Reported duration is less than one week, skin tone: lay graders estimated 3 on the MST, symptoms reported: itching, an image taken at an angle, the arm is involved: 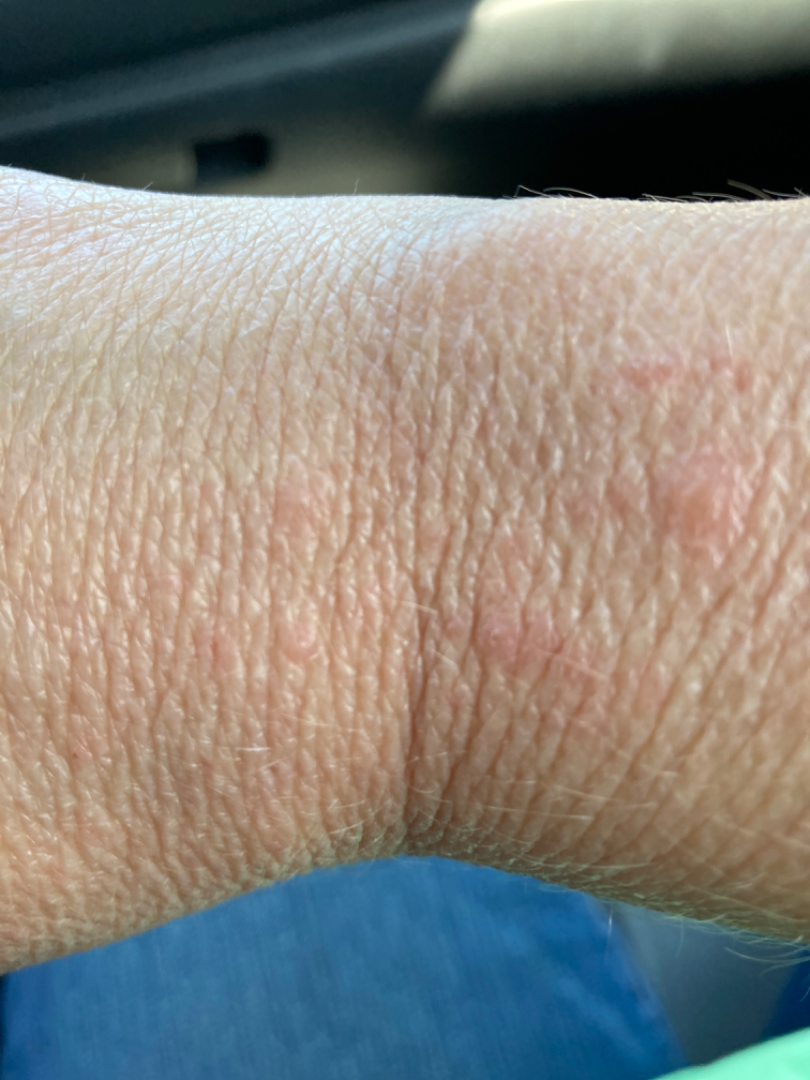  assessment: could not be assessed